A dermatoscopic image of a skin lesion: 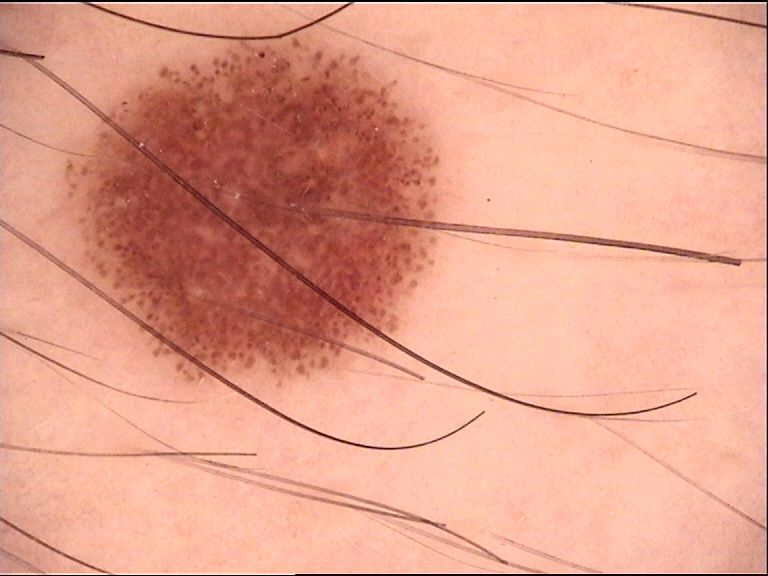{
  "diagnosis": {
    "name": "dysplastic junctional nevus",
    "code": "jd",
    "malignancy": "benign",
    "super_class": "melanocytic",
    "confirmation": "expert consensus"
  }
}